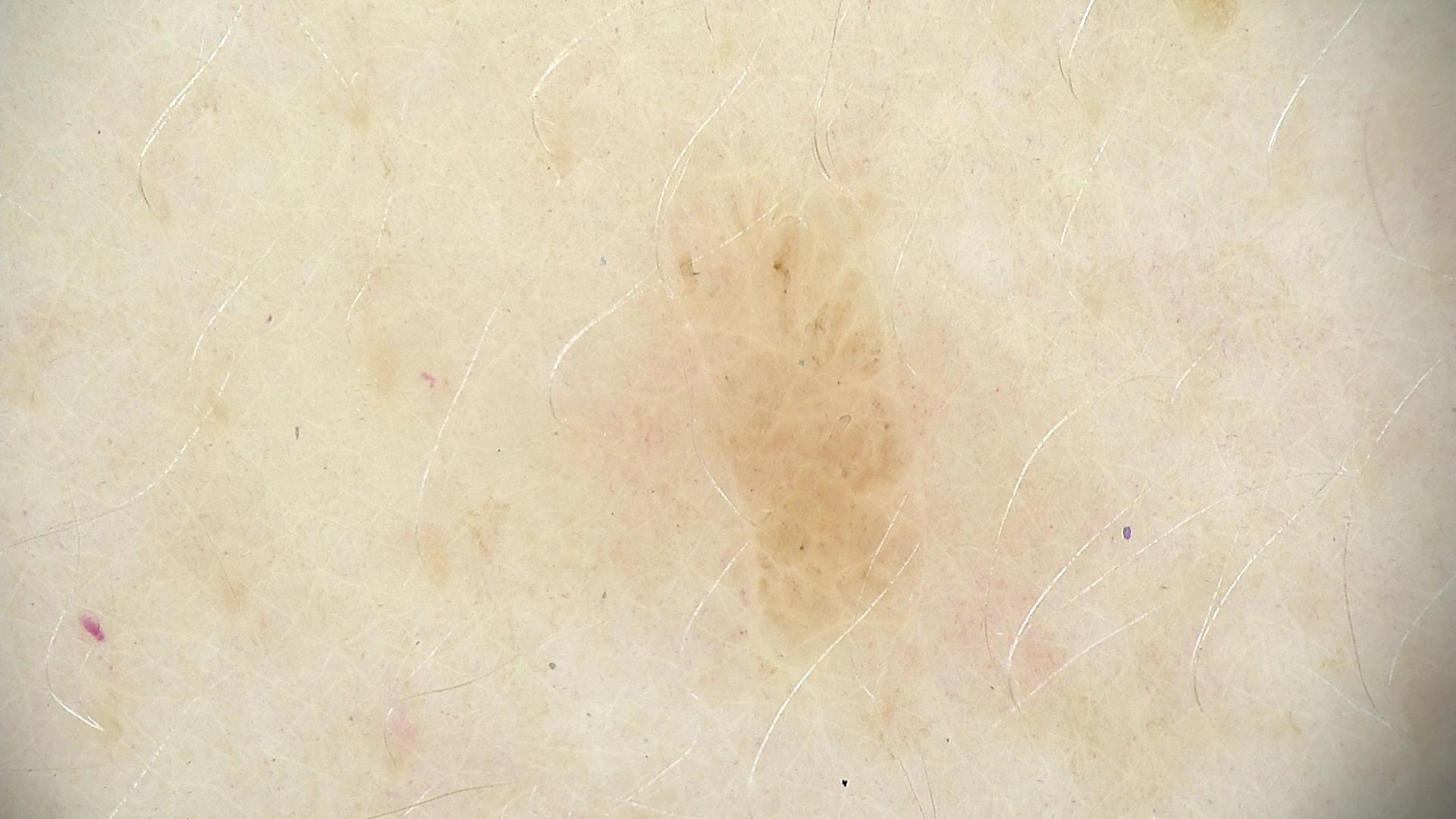<dermoscopy>
<image>dermatoscopy</image>
<lesion_type>
<main_class>keratinocytic</main_class>
</lesion_type>
<diagnosis>
<name>seborrheic keratosis</name>
<code>sk</code>
<malignancy>benign</malignancy>
<super_class>non-melanocytic</super_class>
<confirmation>expert consensus</confirmation>
</diagnosis>
</dermoscopy>